The lesion involves the leg · this is a close-up image · the subject is 30–39, male · no constitutional symptoms were reported · the patient indicates the condition has been present for more than five years — 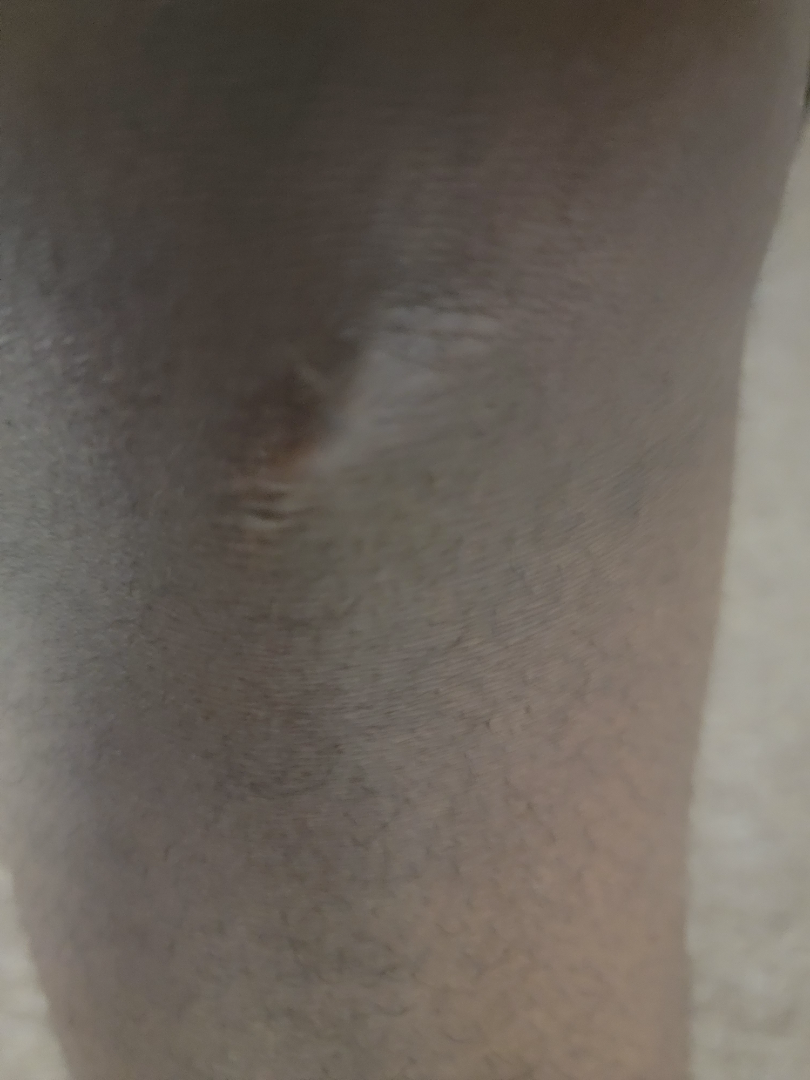Reviewed remotely by three dermatologists: favoring Scar Condition; also on the differential is Anetoderma.